The photo was captured at a distance; the affected area is the back of the torso; male subject, age 30–39 — 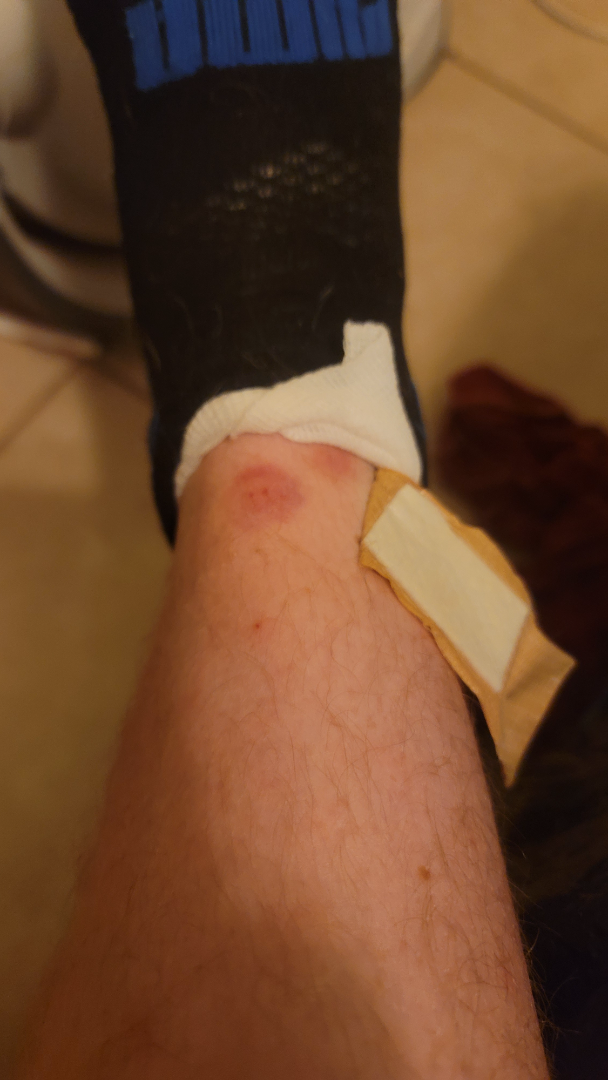reported symptoms: pain, itching, darkening, burning and bothersome appearance | patient's own categorization: a rash | present for: one to three months | surface texture: fluid-filled, flat and raised or bumpy | systemic symptoms: none reported | dermatologist impression: ecchymoses (0.41); Insect Bite (0.22); Pigmented purpuric eruption (0.18); Allergic Contact Dermatitis (0.18).